On a questionnaire the patient reported a personal history of cancer, no sunbed use, and no immunosuppression. The patient says their skin tans without first burning. Few moles overall by the patient's own estimate. Acquired for a research image collection, with no referral diagnosis:
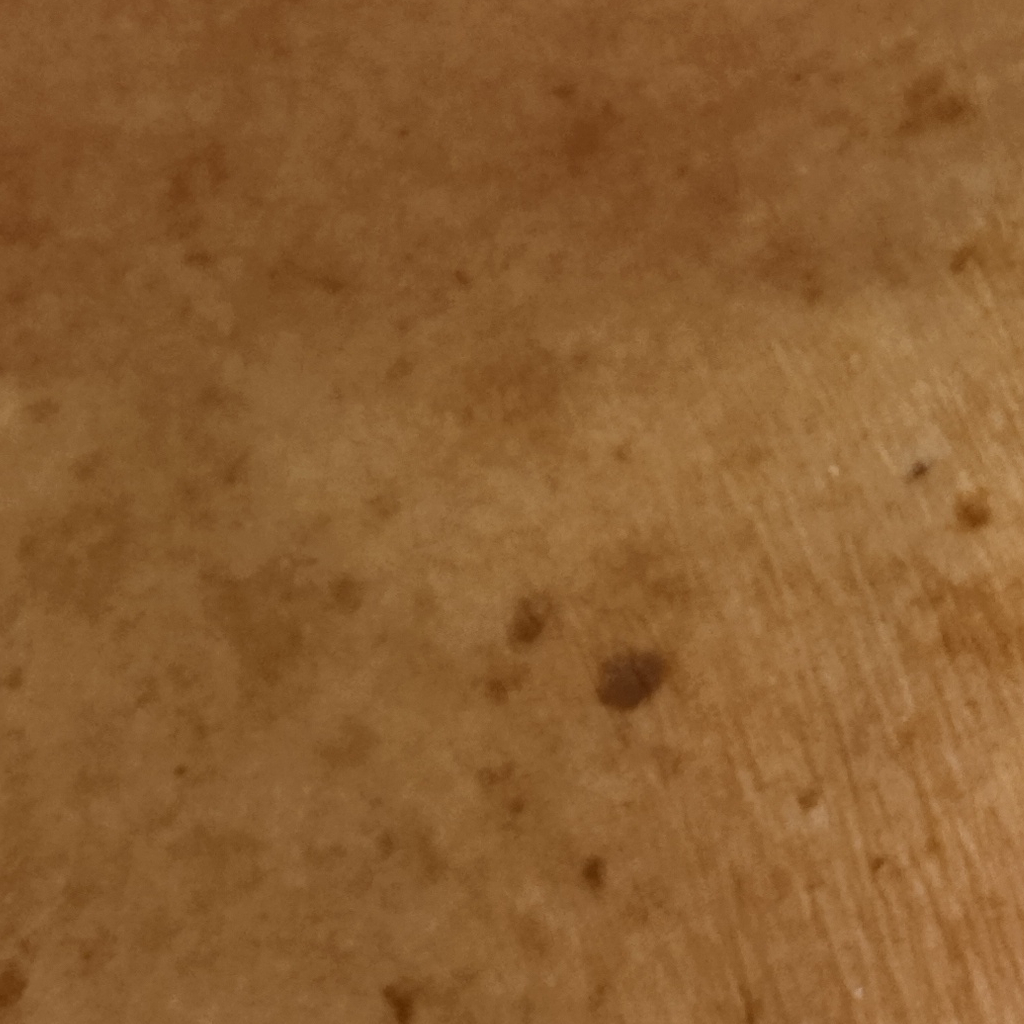Located on the torso.
Measuring roughly 4.6 mm.
The dermatologists' assessment was a seborrheic keratosis.